The subject is 60–69, male. This is a close-up image.
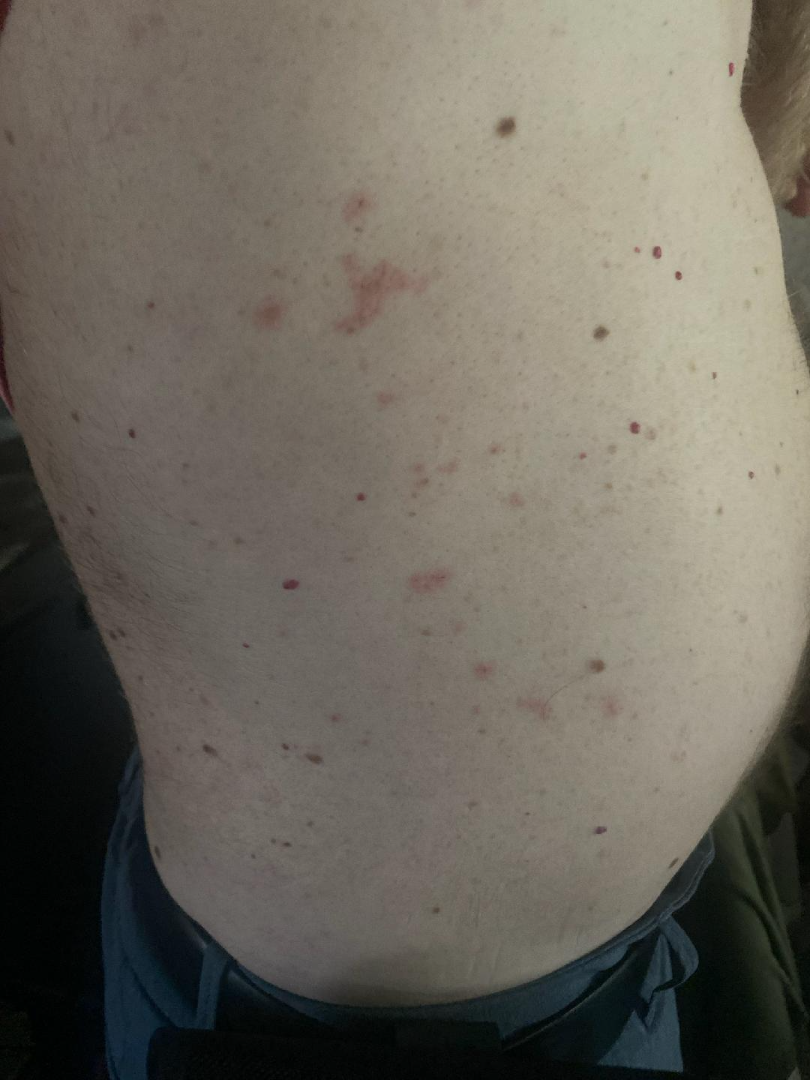Q: Could the case be diagnosed?
A: unable to determine
Q: Constitutional symptoms?
A: none reported
Q: Duration?
A: about one day
Q: How does the lesion feel?
A: flat
Q: Patient's own categorization?
A: a rash